A dermoscopy image of a single skin lesion.
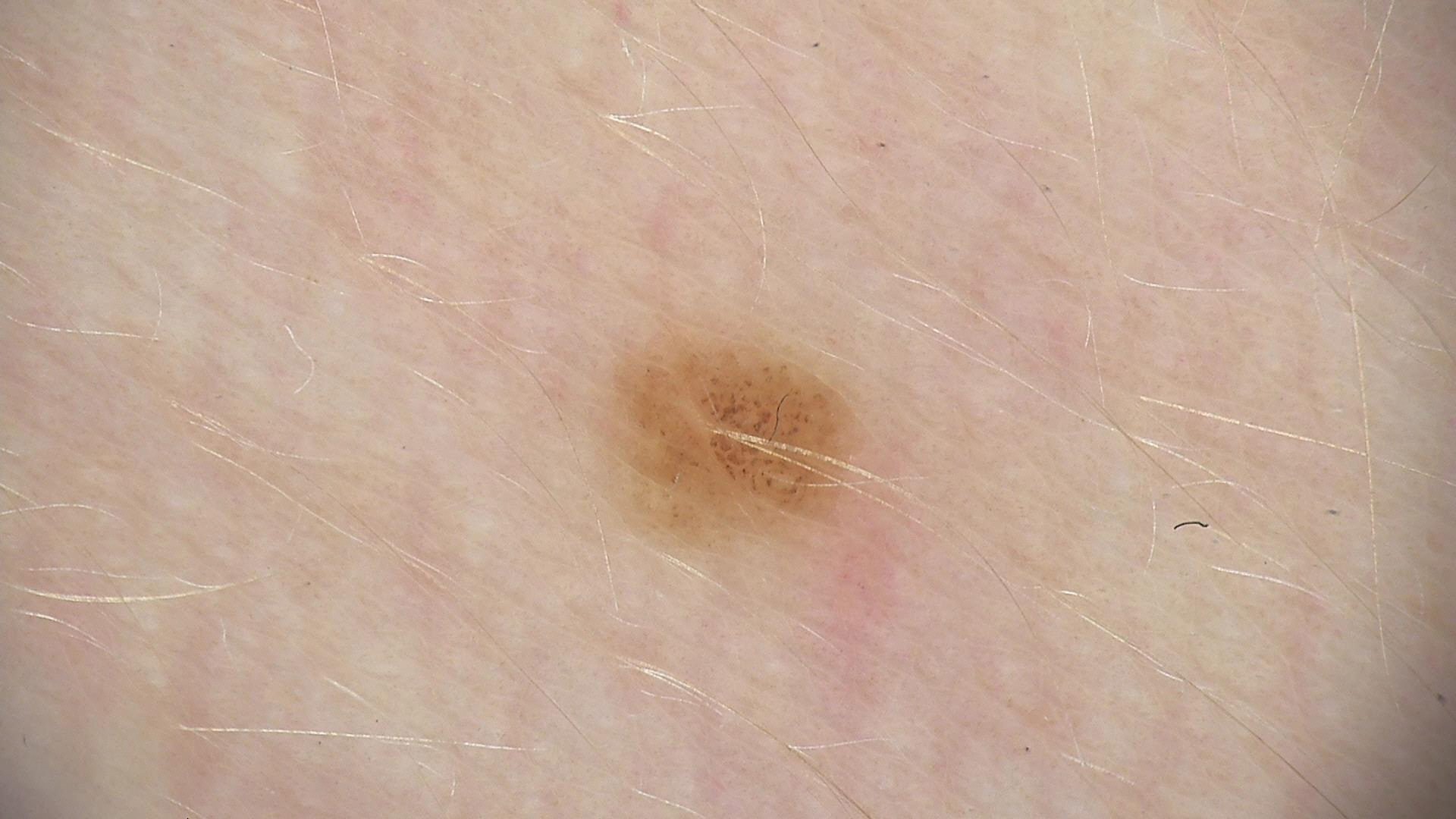{
  "diagnosis": {
    "name": "compound nevus",
    "code": "cb",
    "malignancy": "benign",
    "super_class": "melanocytic",
    "confirmation": "expert consensus"
  }
}